A dermatoscopic image of a skin lesion.
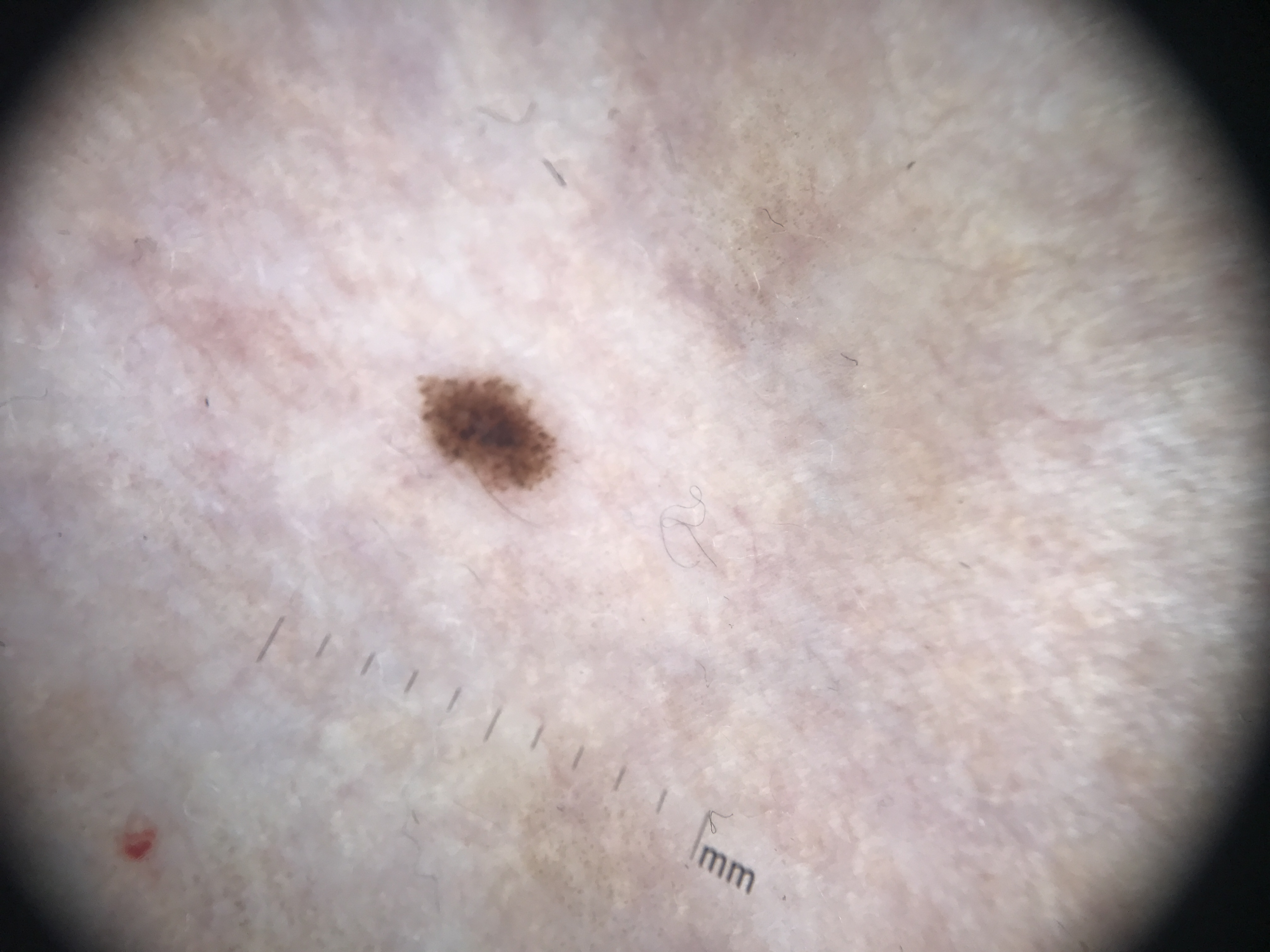Consistent with a benign lesion — a dysplastic junctional nevus.